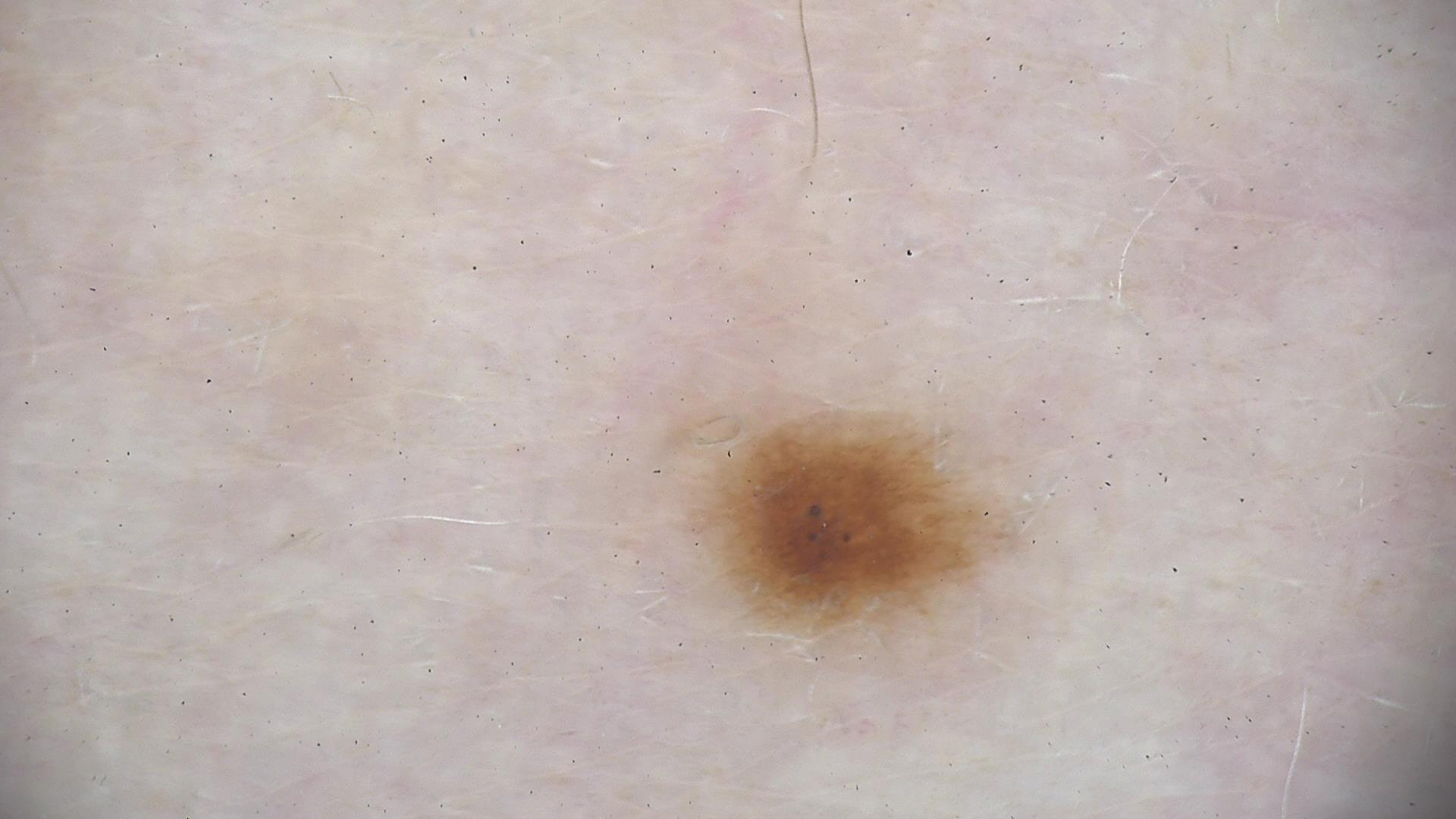A dermoscopy image of a single skin lesion. Classified as a dysplastic junctional nevus.